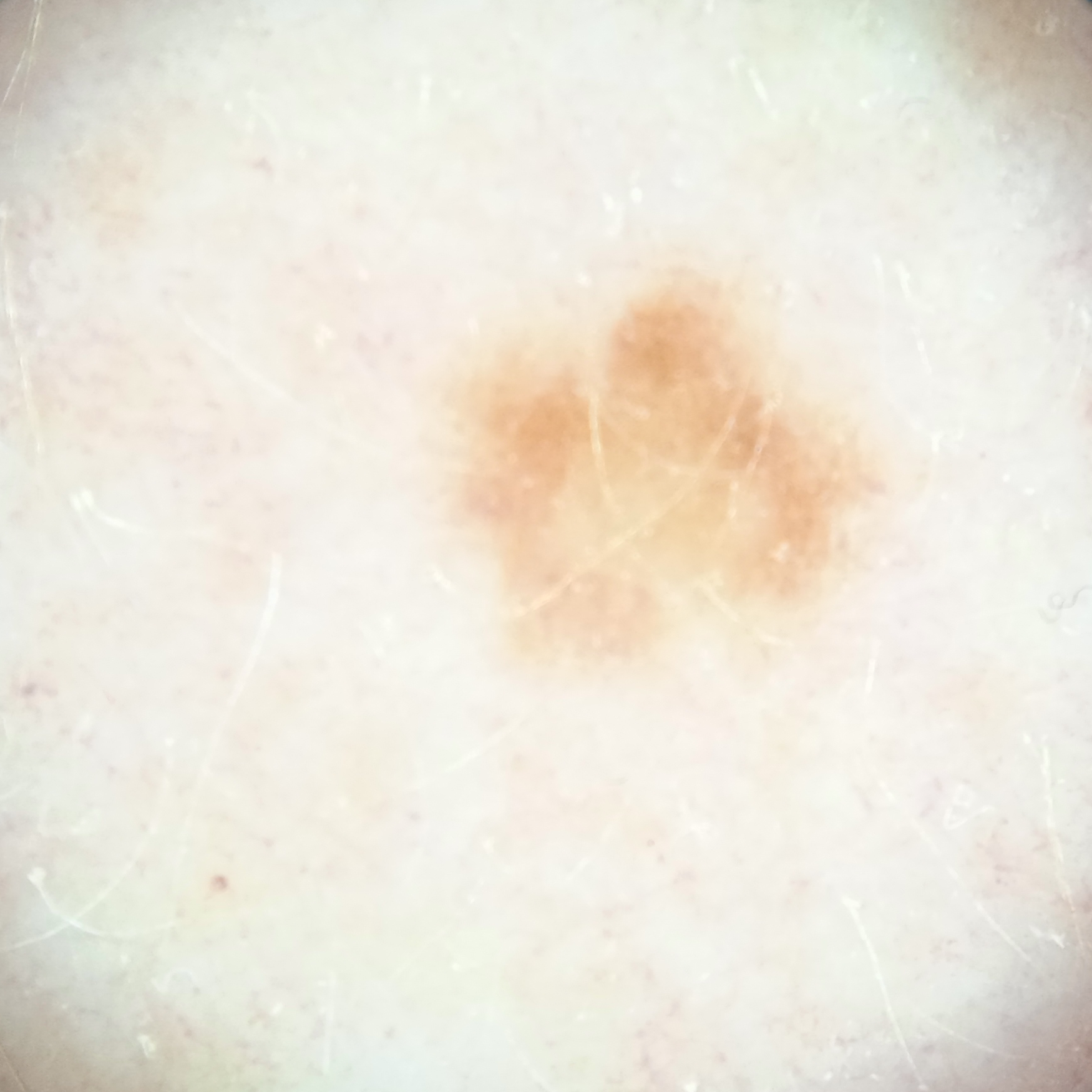The lesion was assessed as an atypical (dysplastic) nevus.